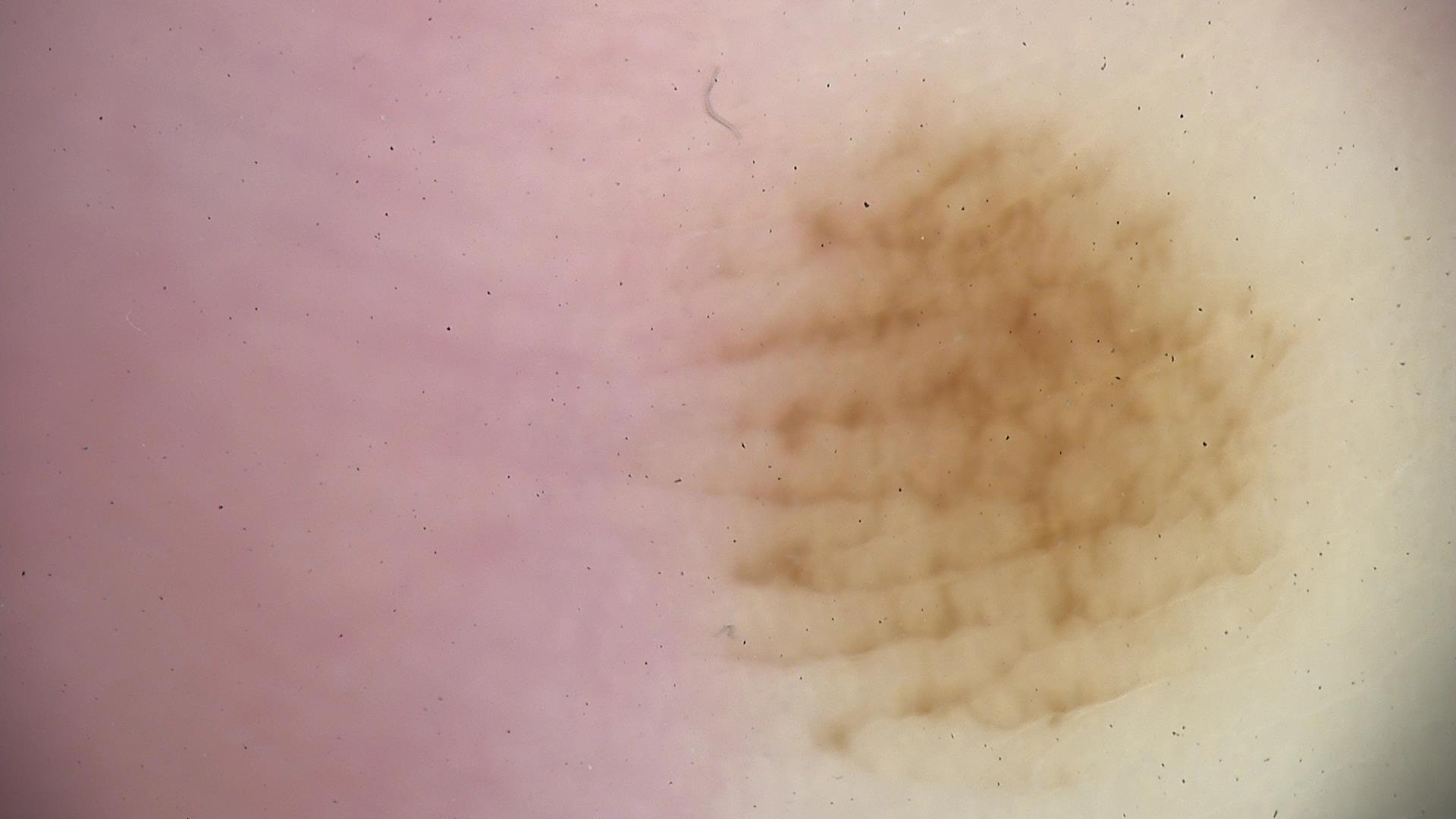image = dermoscopy | class = acral dysplastic junctional nevus (expert consensus).